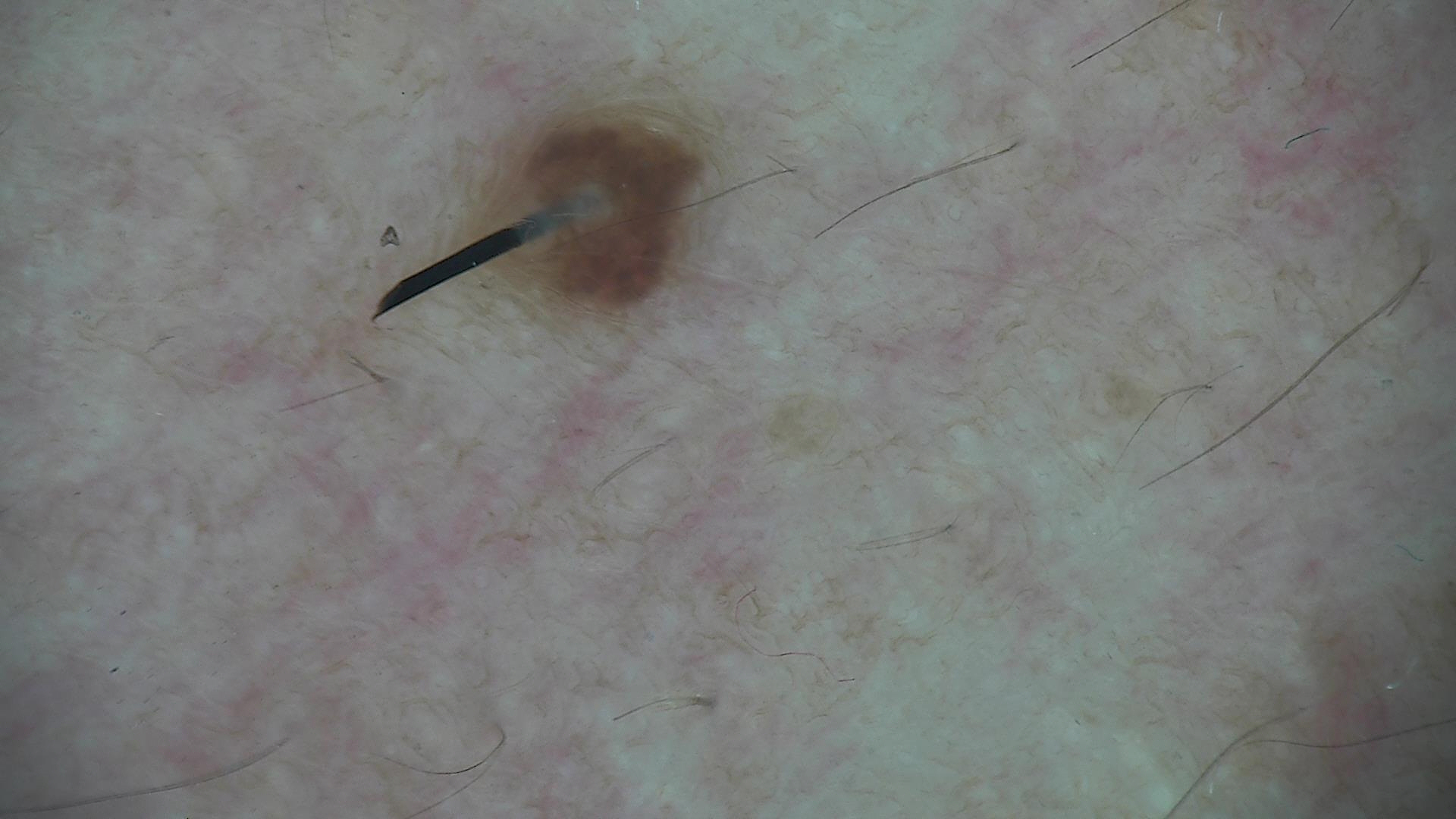A dermoscopy image of a single skin lesion.
The architecture is that of a banal lesion.
Consistent with a compound nevus.